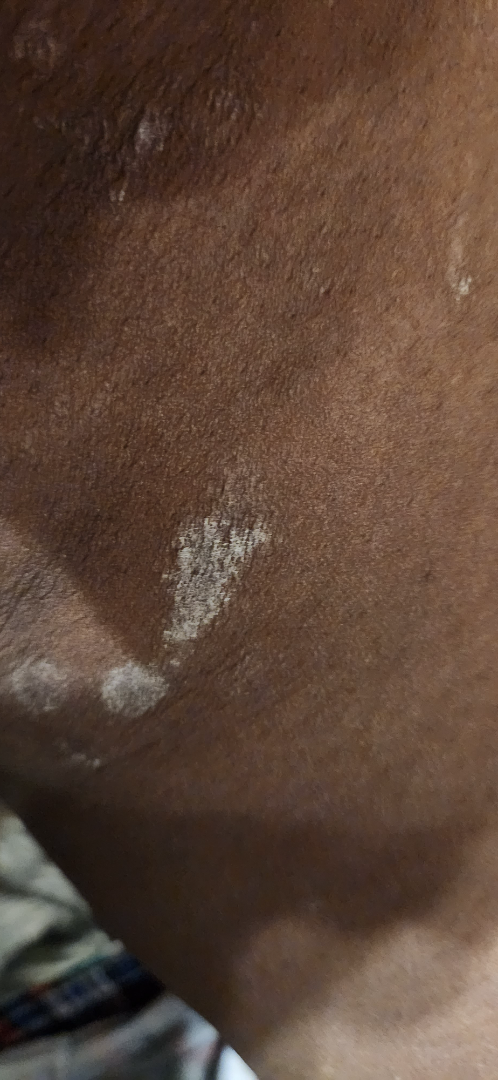Findings:
– assessment — indeterminate